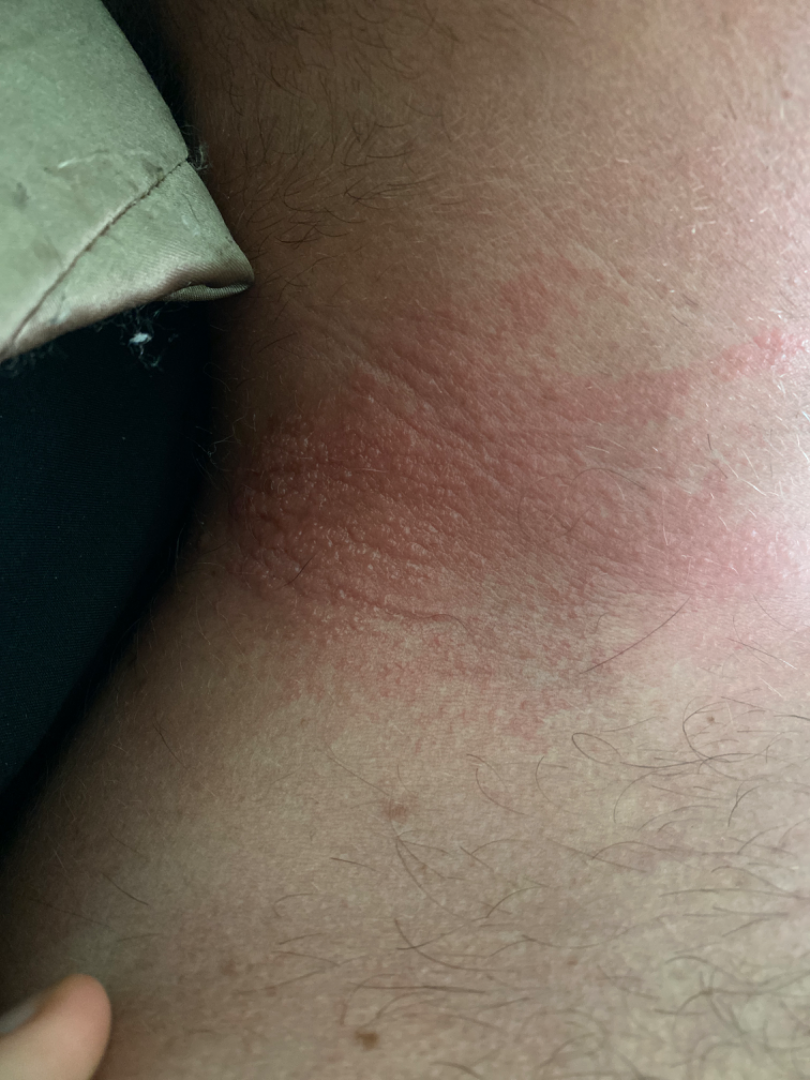  assessment: not assessable
  skin_tone:
    fitzpatrick: IV
    monk_skin_tone:
      - 2
      - 3
  shot_type: close-up